A contact-polarized dermoscopy image of a skin lesion · a female subject approximately 35 years of age:
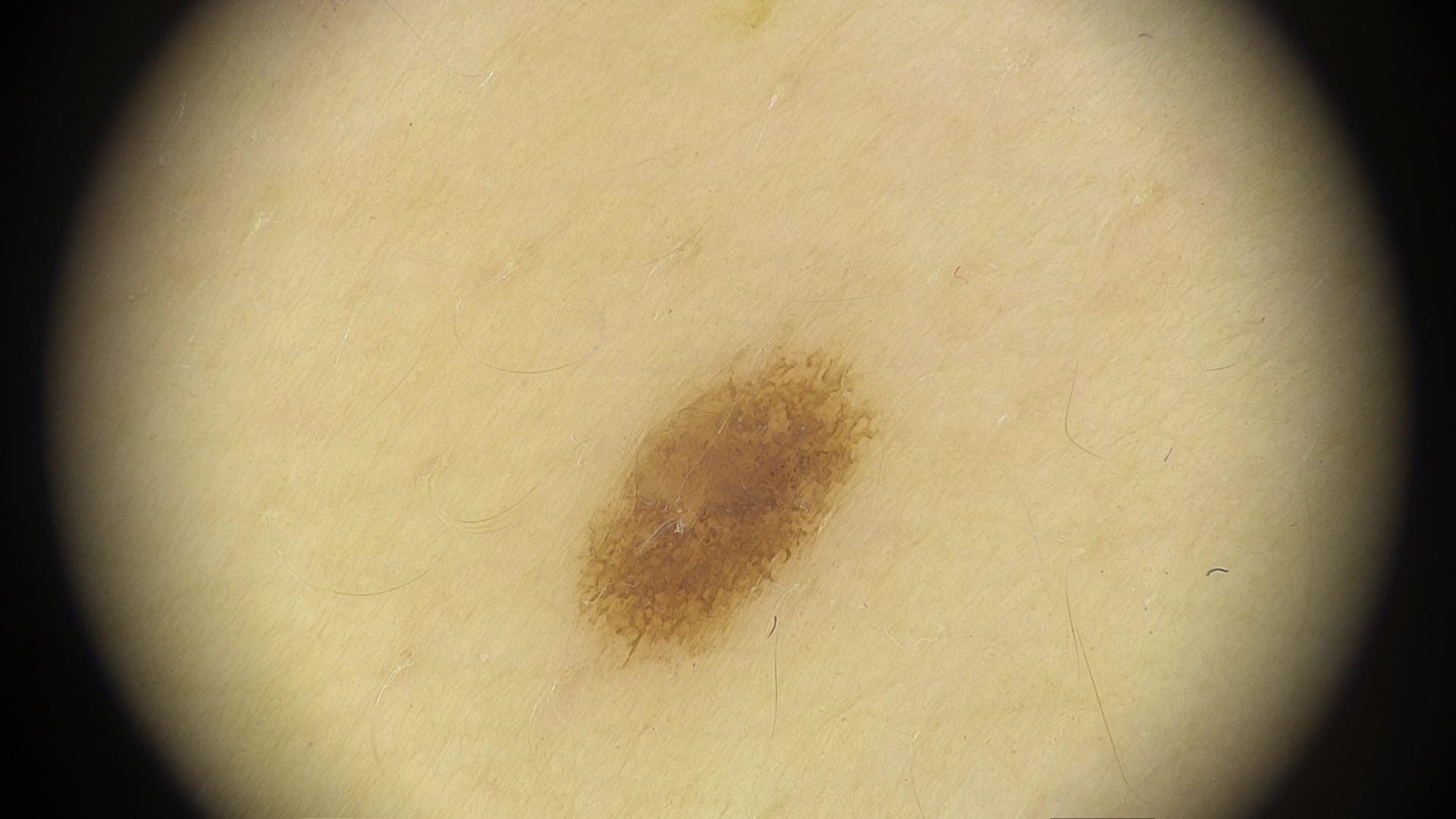The diagnostic impression was a benign lesion — a nevus.